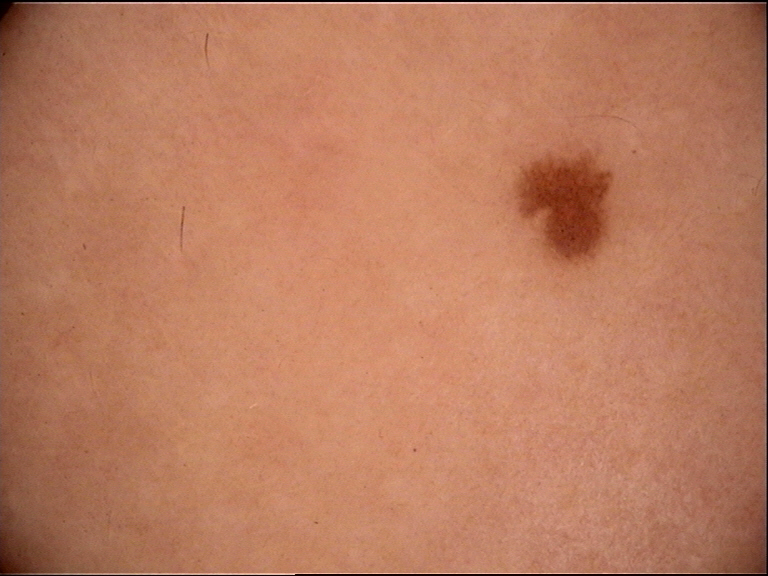Q: What is the diagnosis?
A: junctional nevus (expert consensus)